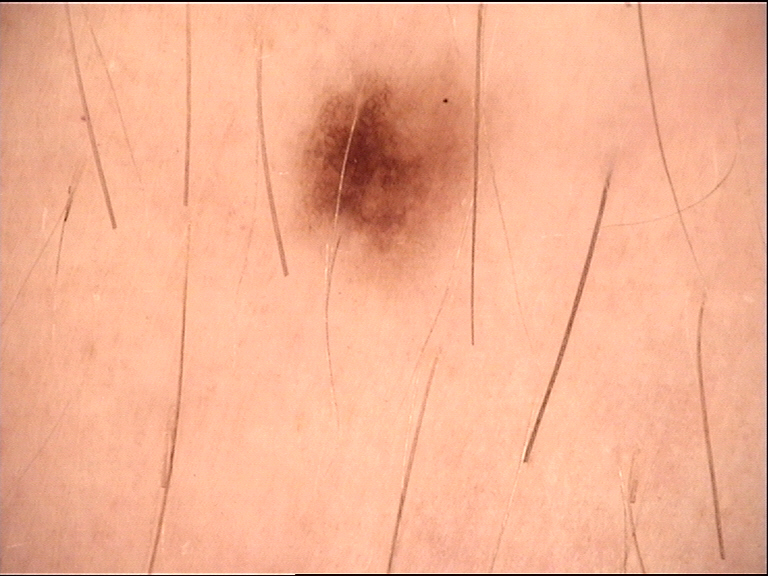assessment — dysplastic junctional nevus (expert consensus).